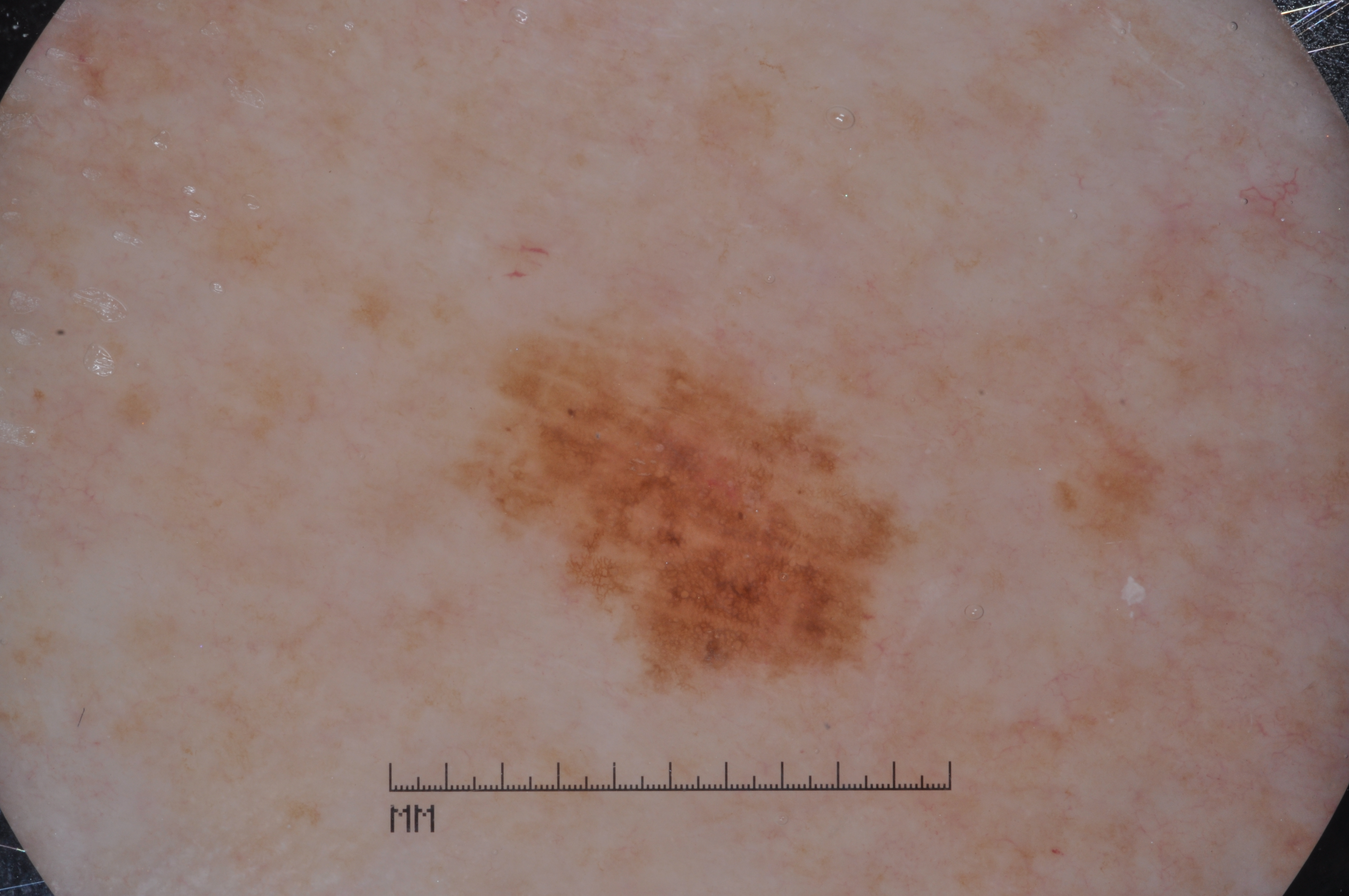  image:
    modality: dermoscopy
  lesion_location:
    bbox_xyxy:
      - 474
      - 337
      - 896
      - 679
  diagnosis:
    name: melanoma
    malignancy: malignant
    lineage: melanocytic
    provenance: histopathology